A skin lesion imaged with a dermatoscope.
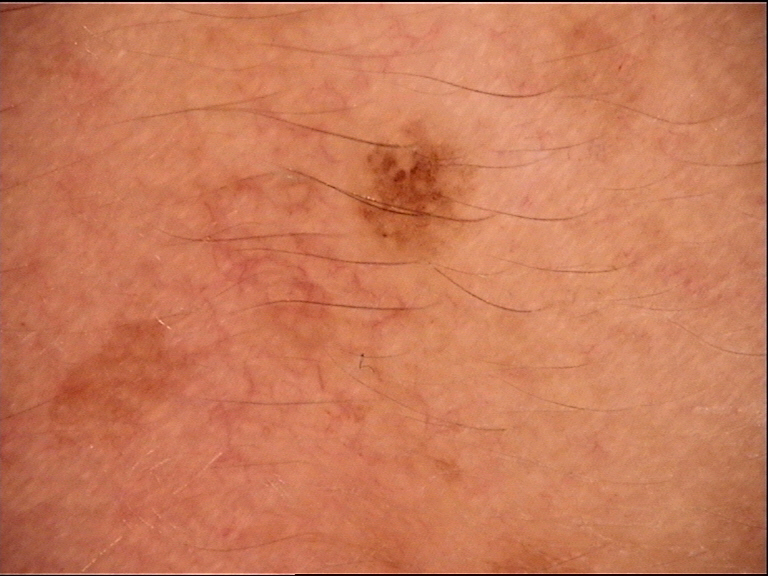  diagnosis:
    name: Miescher nevus
    code: mcb
    malignancy: benign
    super_class: melanocytic
    confirmation: expert consensus